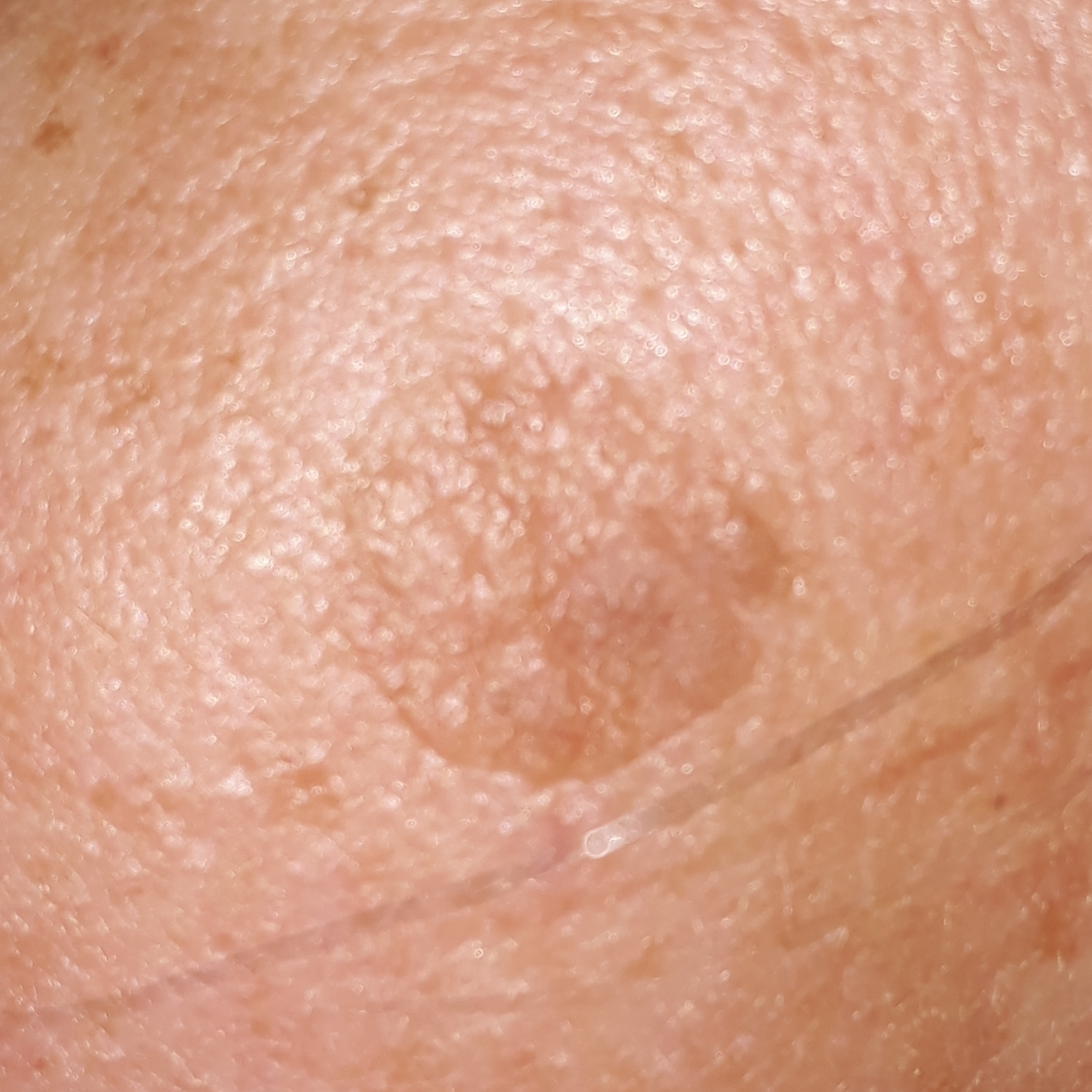image: clinical photo | subject: aged 42 | site: the face | patient-reported symptoms: elevation, growth | impression: seborrheic keratosis (clinical consensus).